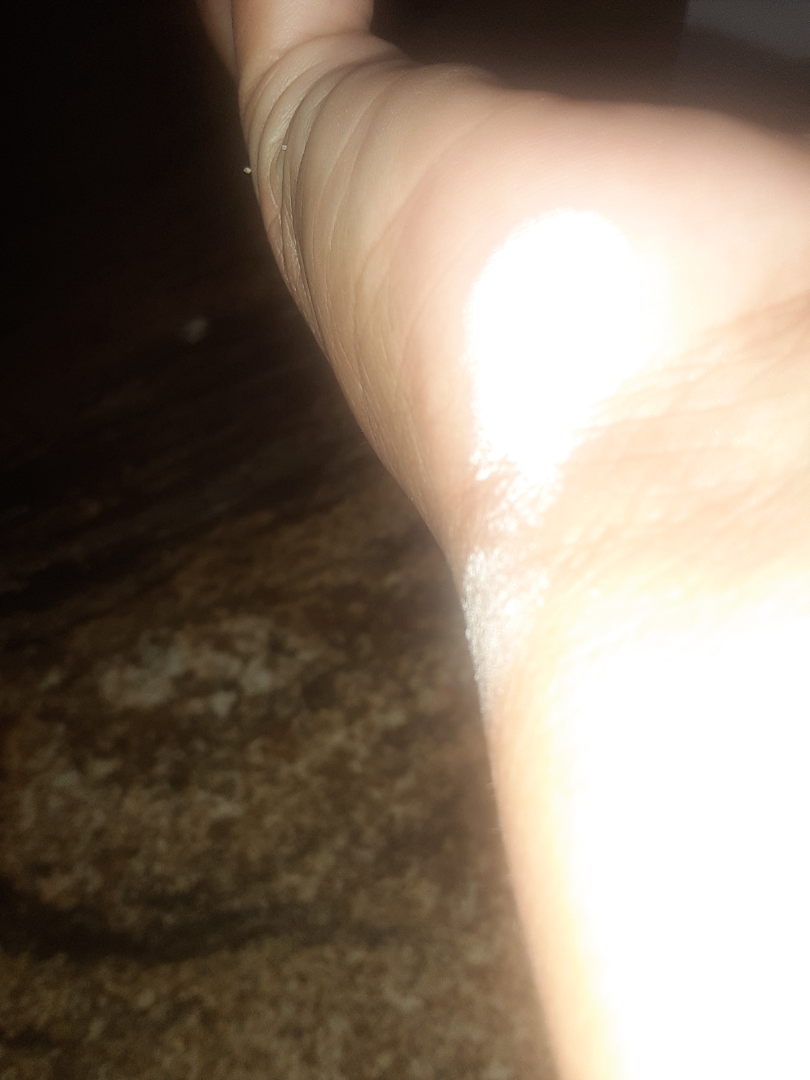assessment = not assessable.